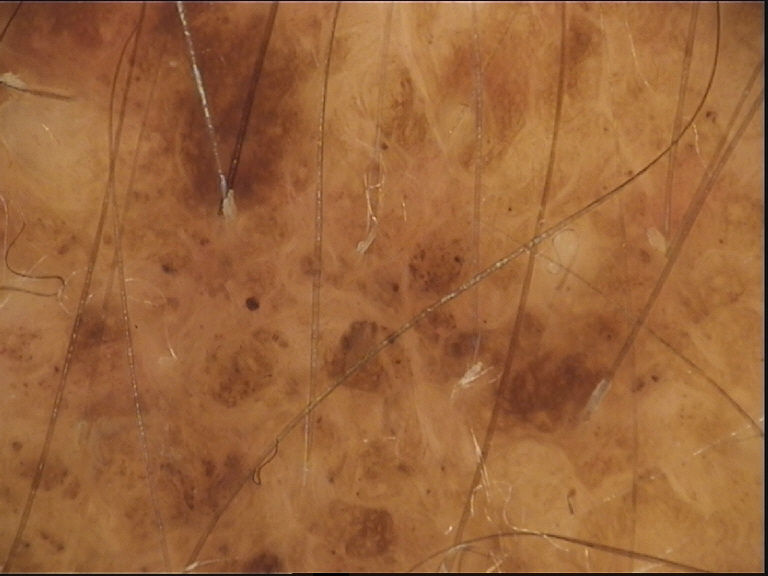<lesion>
<image>dermoscopy</image>
<lesion_type>
<main_class>banal</main_class>
<pattern>compound</pattern>
</lesion_type>
<diagnosis>
<name>congenital compound nevus</name>
<code>ccb</code>
<malignancy>benign</malignancy>
<super_class>melanocytic</super_class>
<confirmation>expert consensus</confirmation>
</diagnosis>
</lesion>